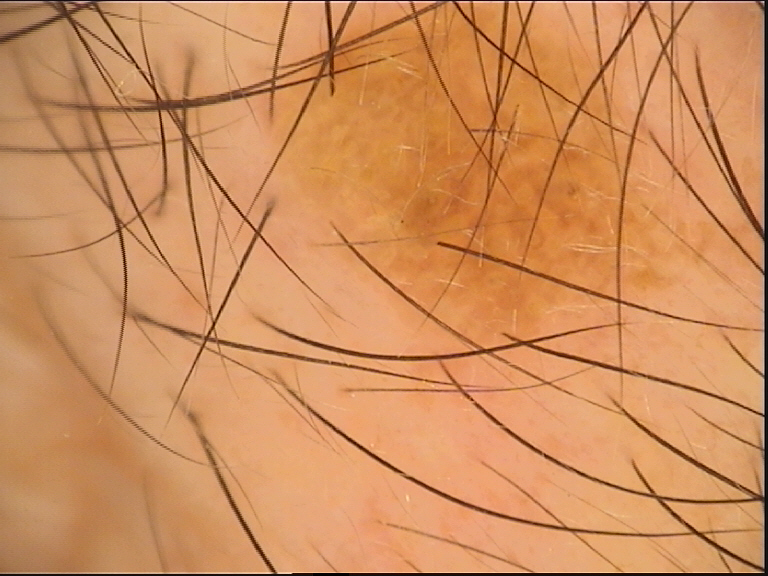A dermoscopic photograph of a skin lesion. The morphology is that of a keratinocytic lesion. Consistent with a benign lesion — a seborrheic keratosis.